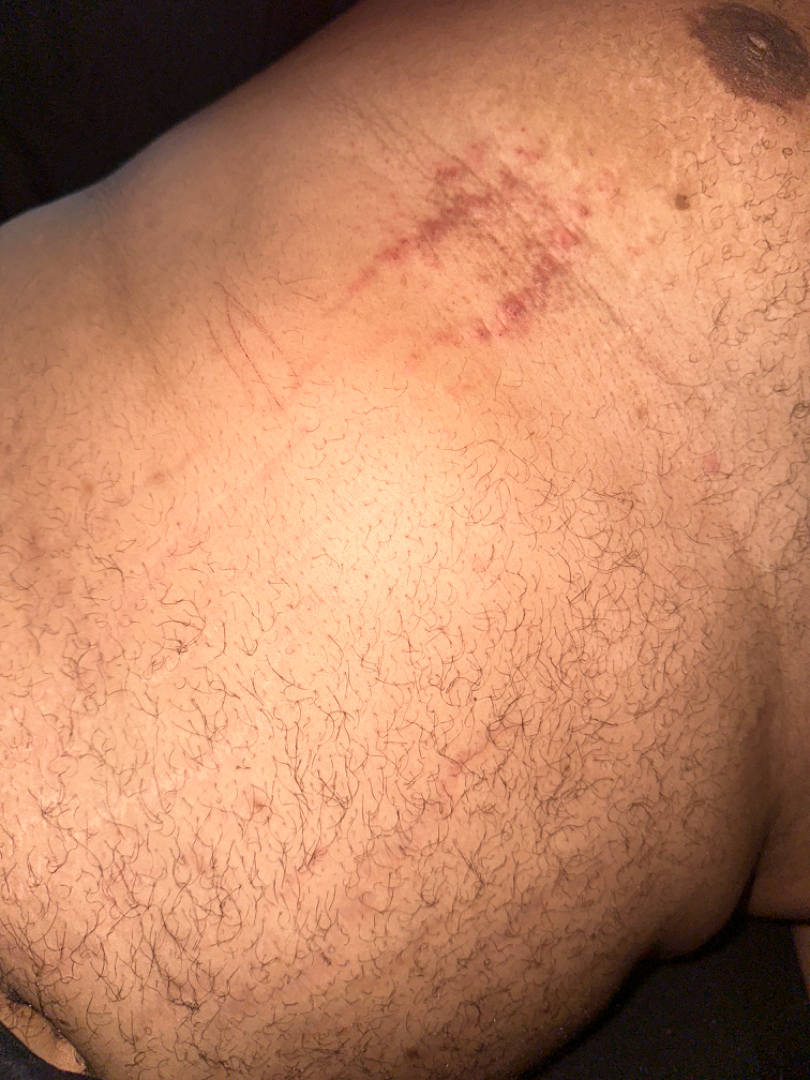The image was not sufficient for the reviewer to characterize the skin condition.
The patient indicates pain, bothersome appearance and itching.
No constitutional symptoms were reported.
The photo was captured at a distance.
The lesion is described as raised or bumpy and rough or flaky.
The patient described the issue as a rash.